The contributor reports the condition has been present for less than one week; no associated systemic symptoms reported; the photo was captured at an angle; the affected area is the front of the torso; the patient is 40–49, female; the lesion is associated with itching: 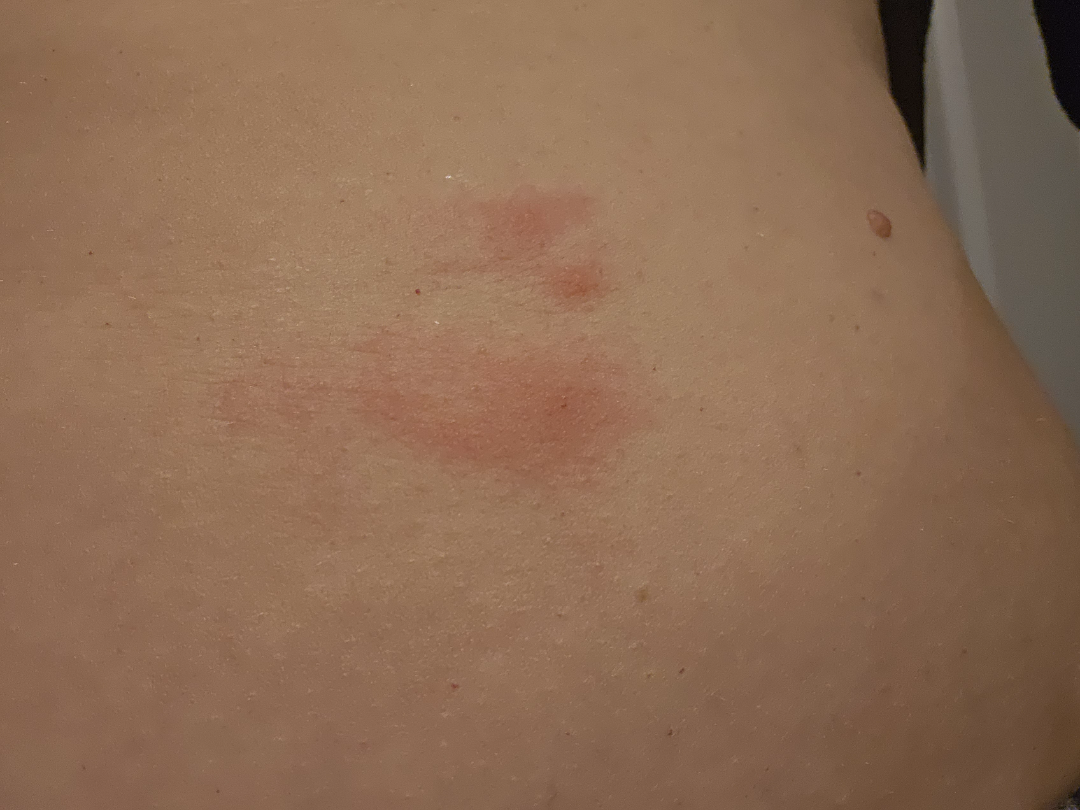Findings:
* assessment — unable to determine